Dermoscopy of a skin lesion: 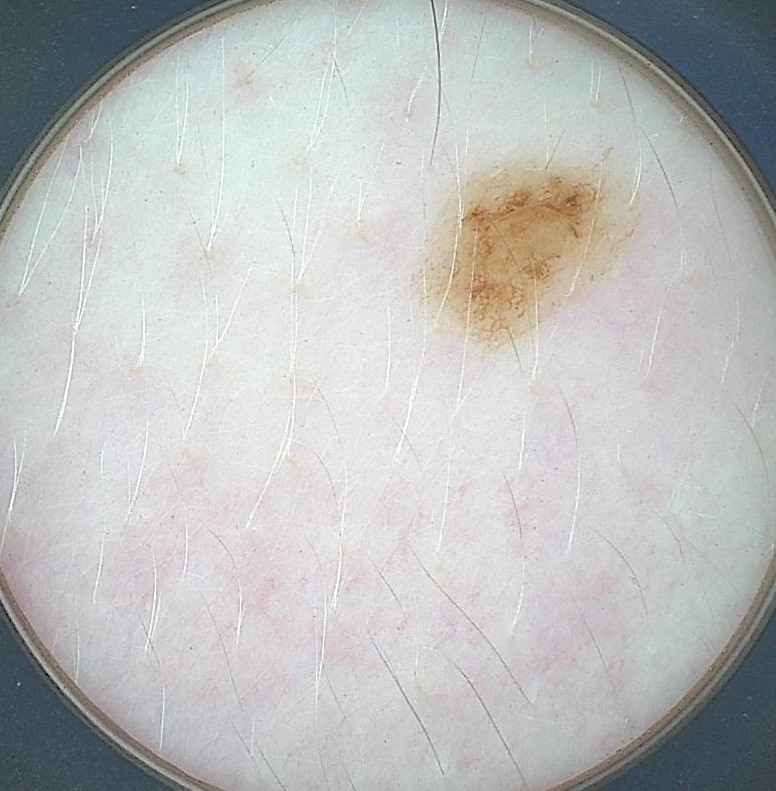label: dysplastic junctional nevus (expert consensus).